Symptoms reported: bothersome appearance · close-up view · the lesion is described as flat · the leg is involved · female patient, age 40–49 · reported duration is one to four weeks.
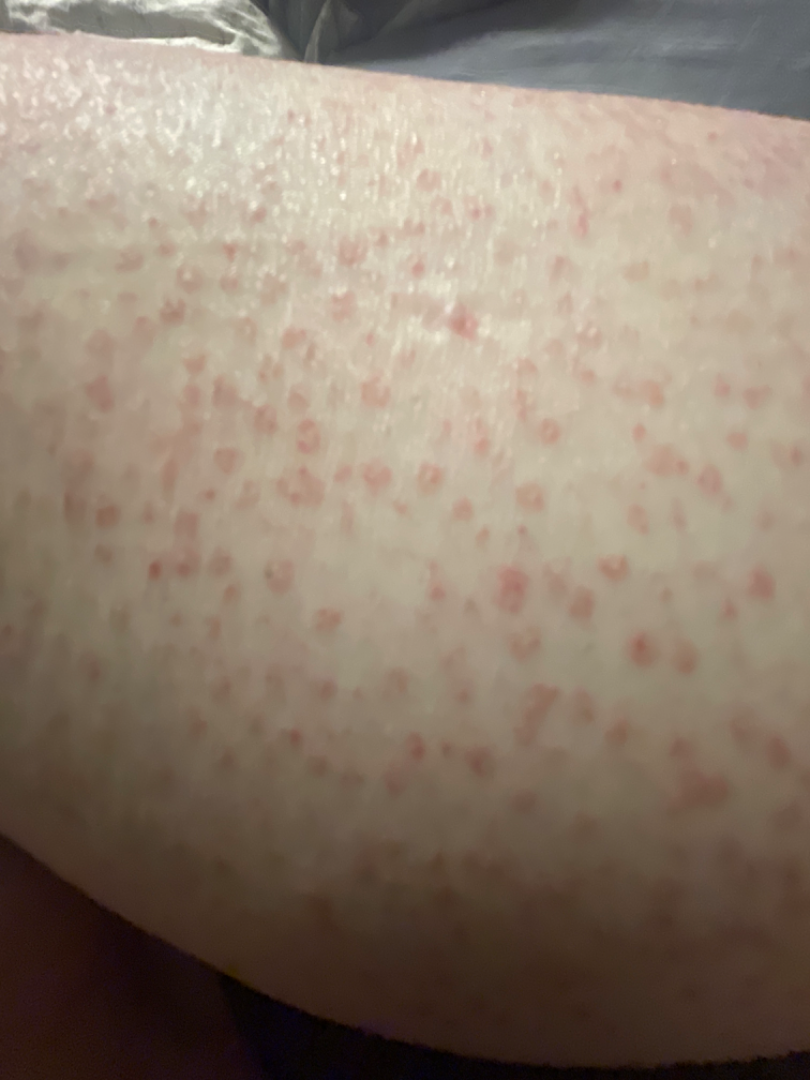Impression: On dermatologist assessment of the image: Leukocytoclastic Vasculitis (weight 0.55); Pigmented purpuric eruption (weight 0.27); Hypersensitivity (weight 0.18).